A dermoscopy image of a single skin lesion: 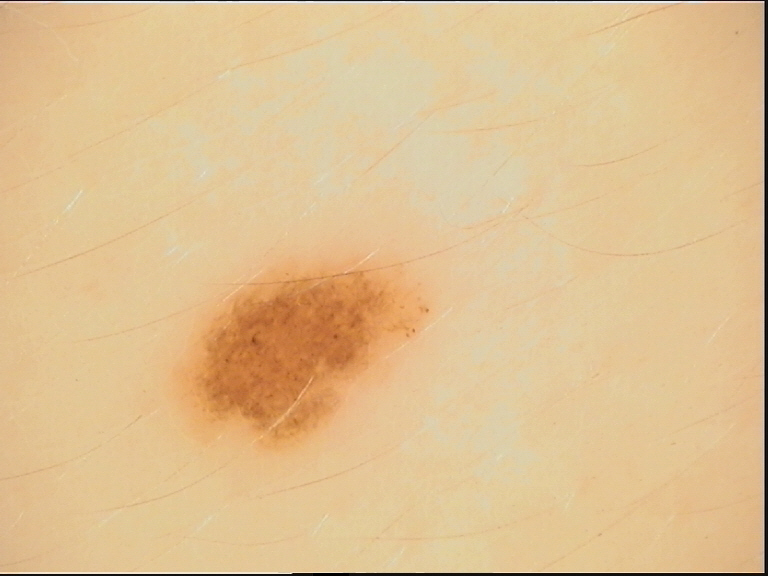The diagnosis was a dysplastic junctional nevus.